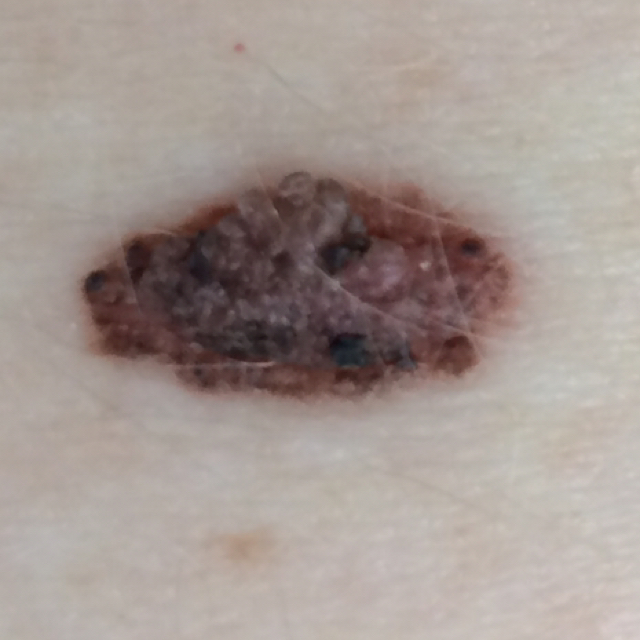{"diagnosis": {"name": "nevus", "code": "NEV", "malignancy": "benign", "confirmation": "clinical consensus"}}